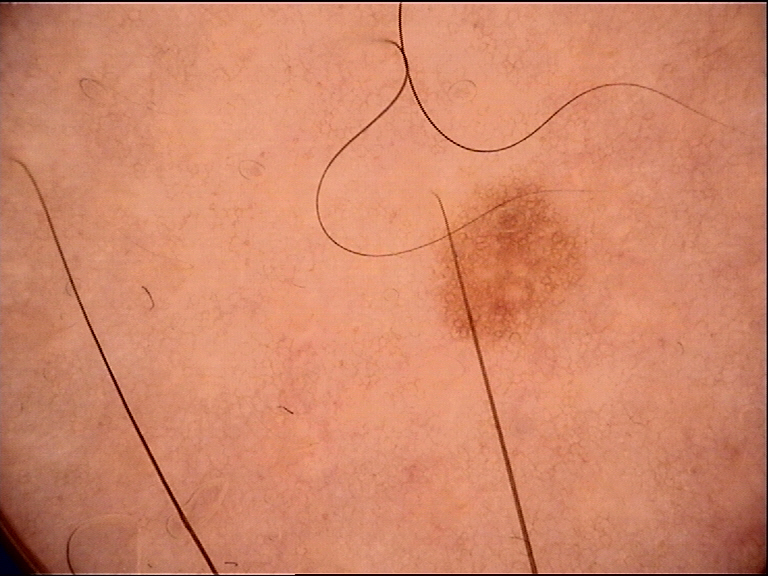A dermoscopic photograph of a skin lesion. The architecture is that of a banal lesion. The diagnostic label was a junctional nevus.